The photo was captured at a distance. Located on the leg:
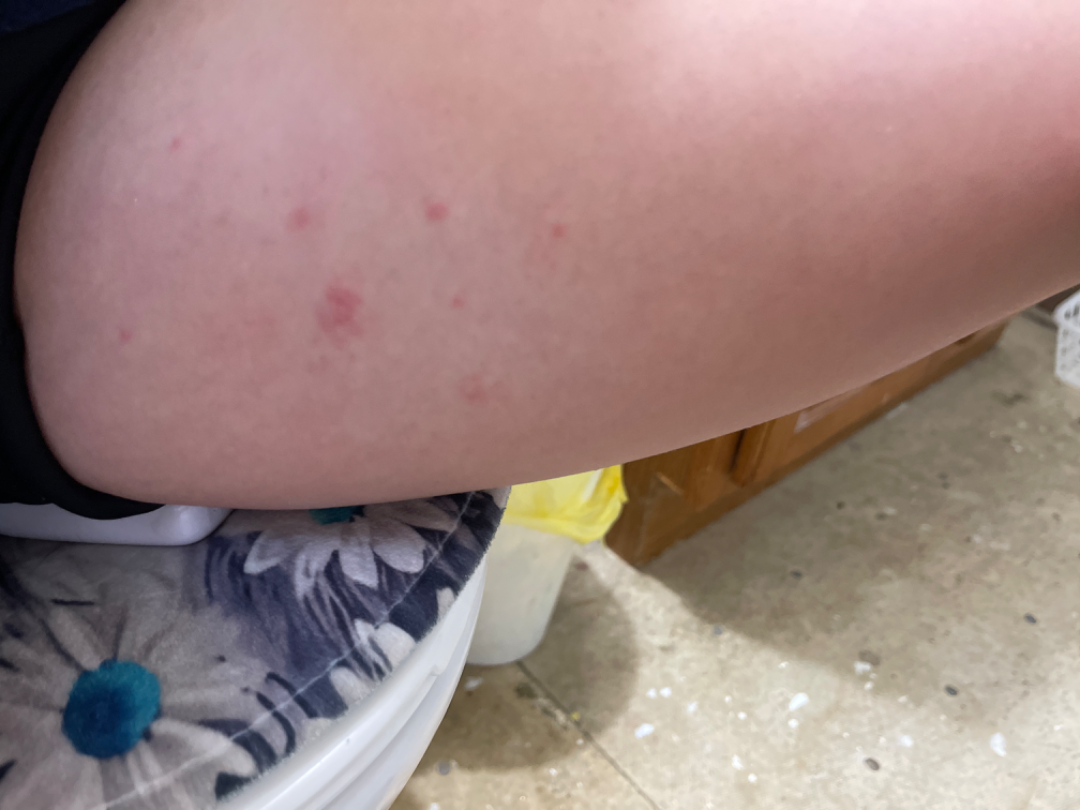Notes:
* differential diagnosis: most consistent with Eczema; also raised was Urticaria